A male patient aged around 75. A clinical photograph of a skin lesion.
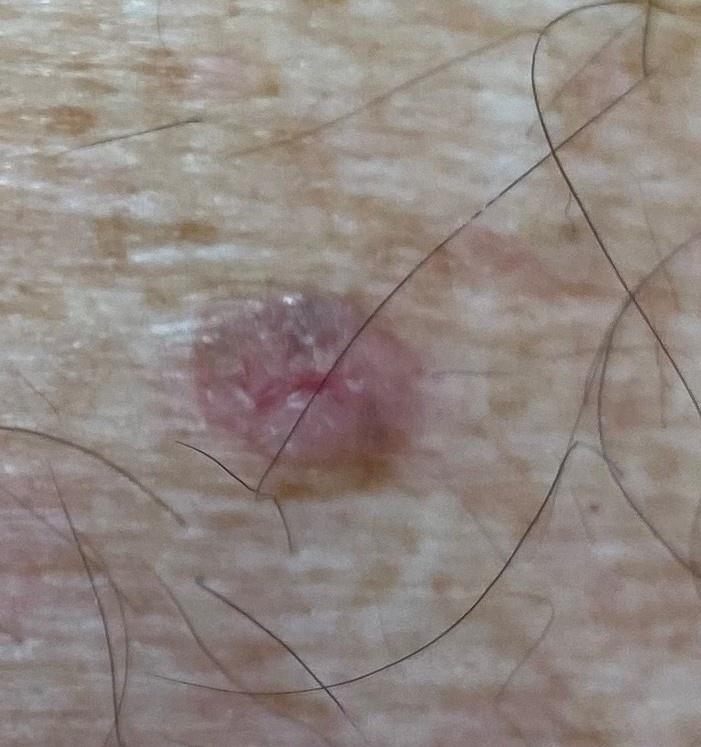{"lesion_location": {"region": "the trunk", "detail": "the posterior trunk"}, "diagnosis": {"name": "Basal cell carcinoma", "malignancy": "malignant", "confirmation": "histopathology", "lineage": "adnexal"}}